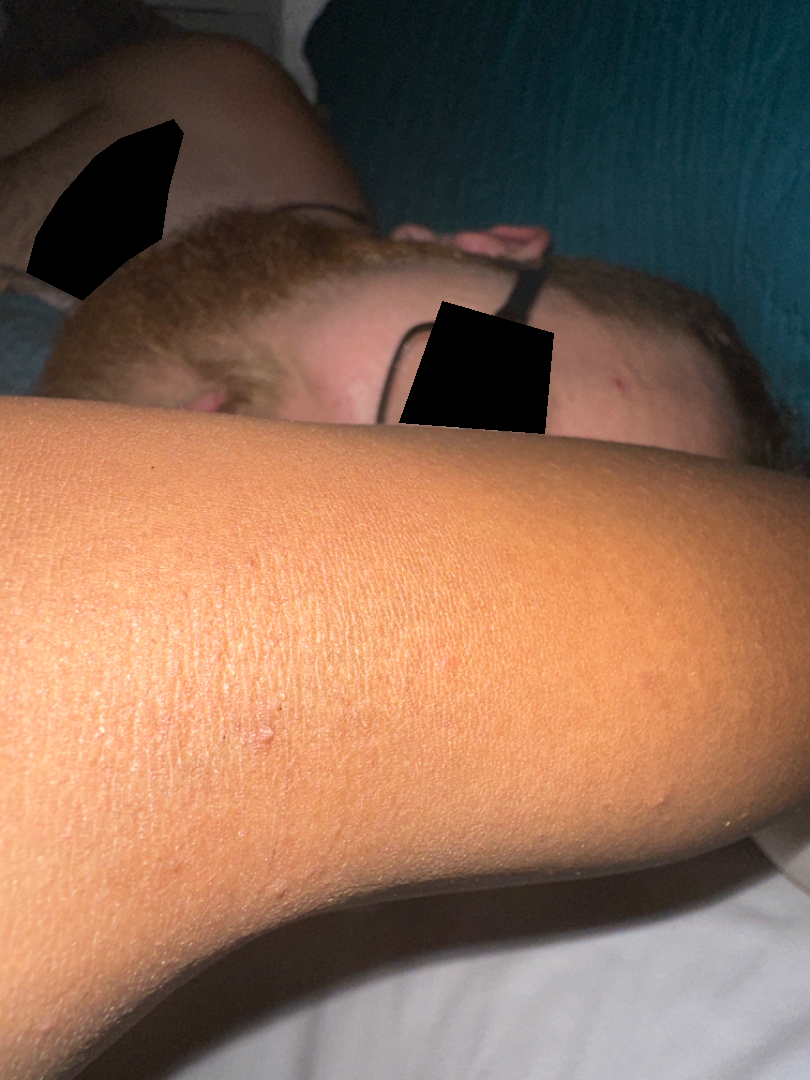Impression: The reviewer was unable to grade this case for skin condition. History: Located on the back of the torso, arm, leg, back of the hand and front of the torso. The contributor is a female aged 18–29. A close-up photograph.